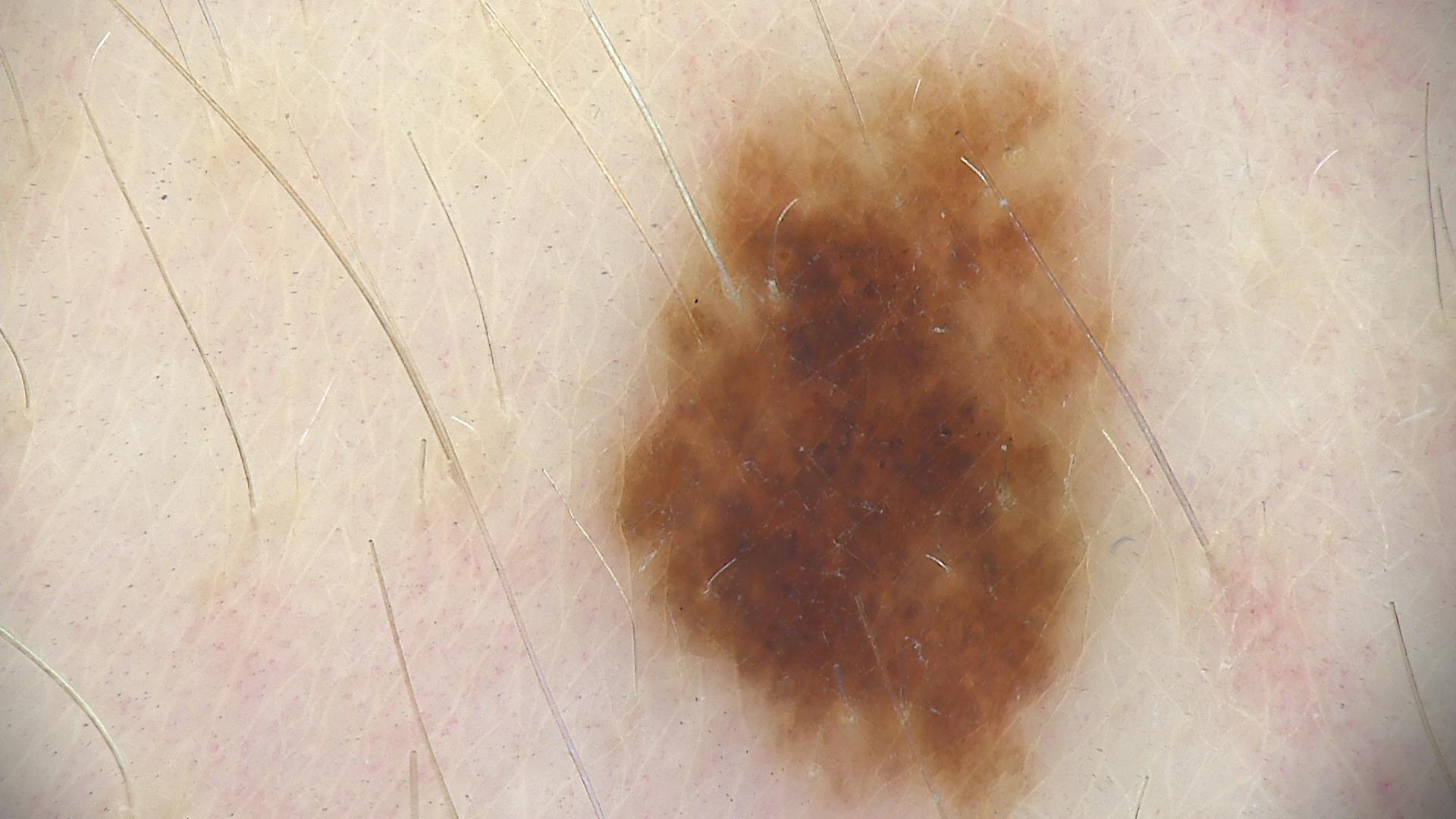diagnosis = dysplastic junctional nevus (expert consensus)